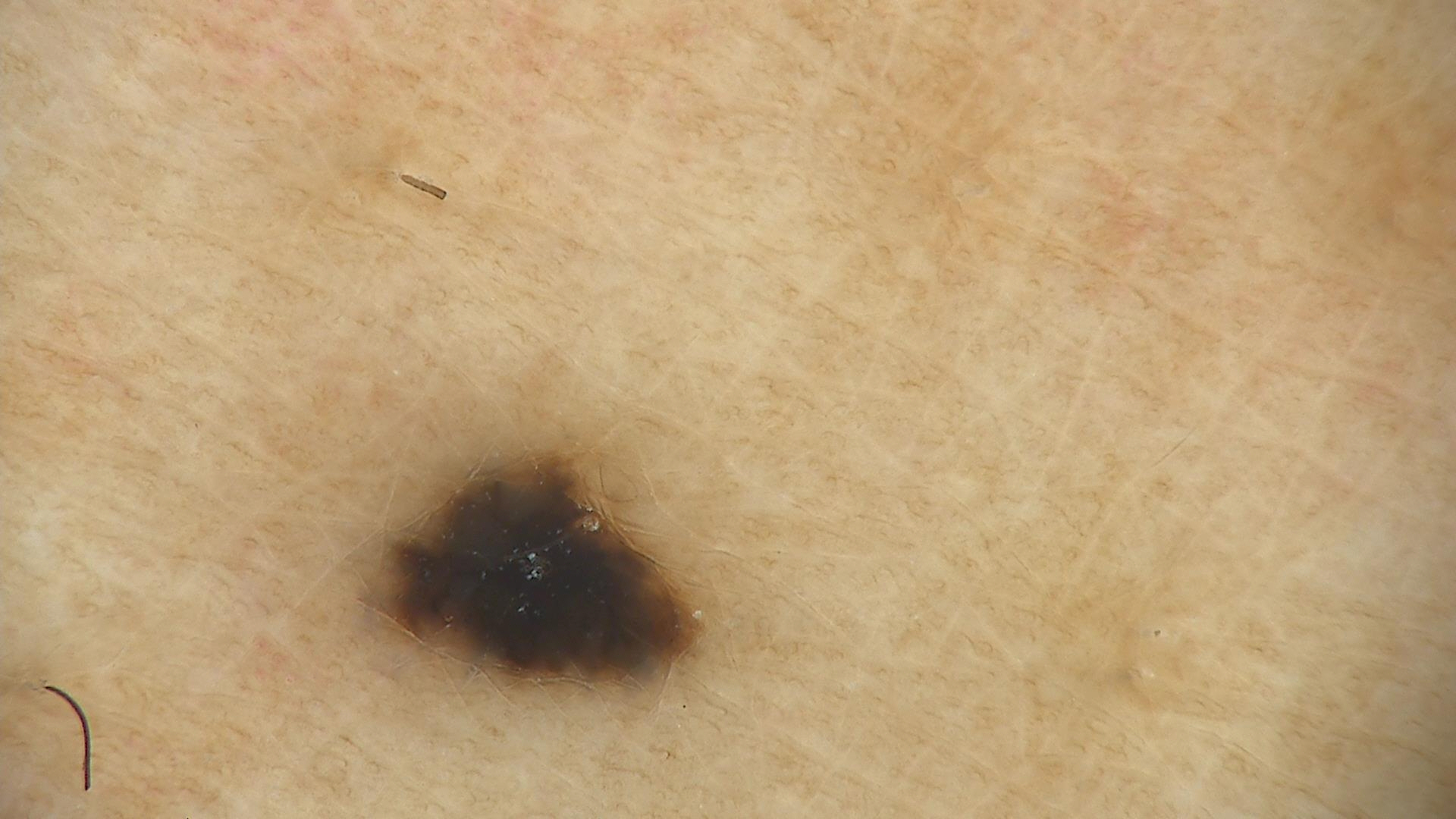Impression:
Diagnosed as a blue nevus.